A dermoscopic photograph of a skin lesion.
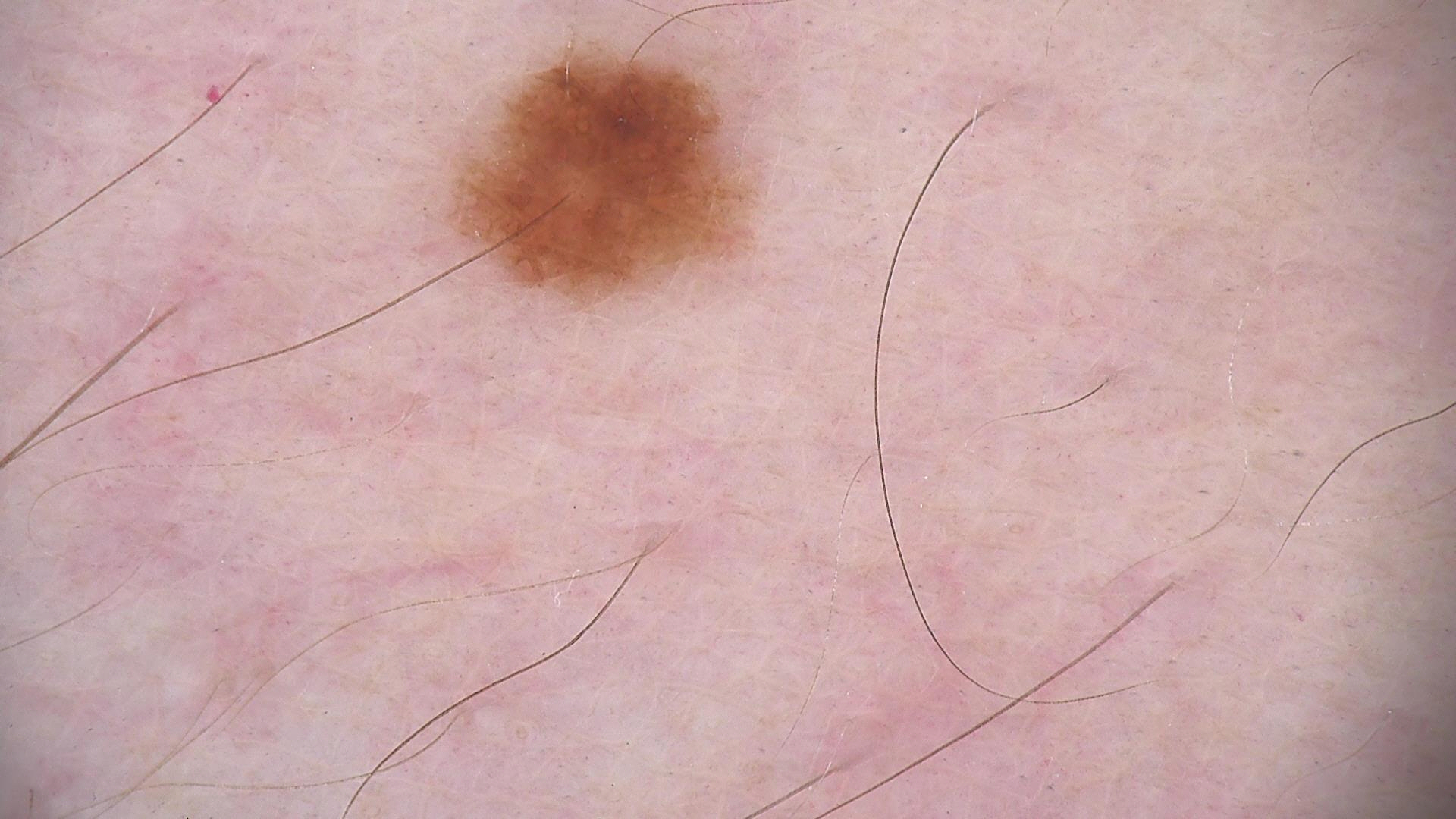The diagnosis was a benign lesion — a dysplastic junctional nevus.